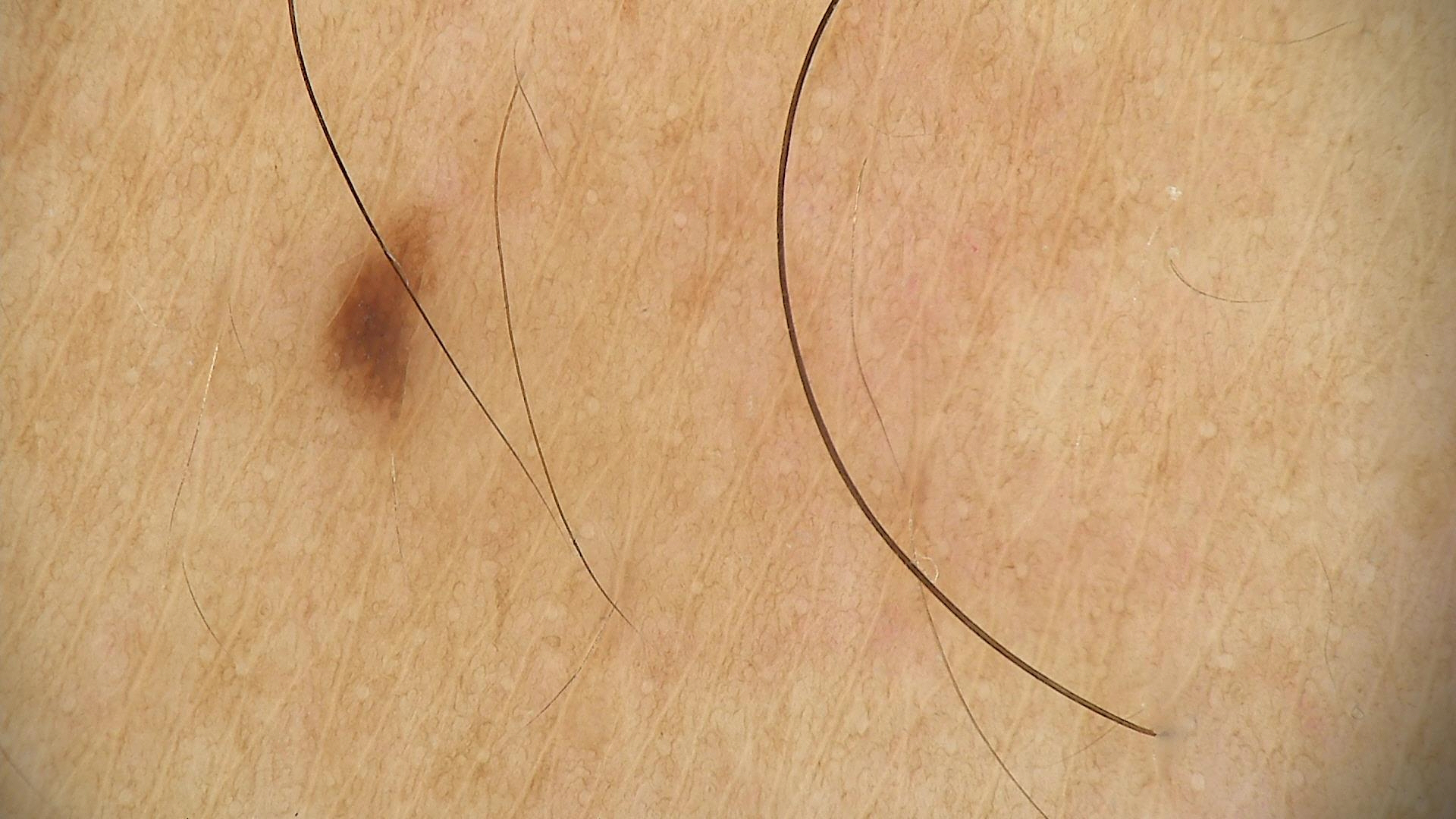  lesion_type:
    main_class: banal
    pattern: junctional
  diagnosis:
    name: junctional nevus
    code: jb
    malignancy: benign
    super_class: melanocytic
    confirmation: expert consensus